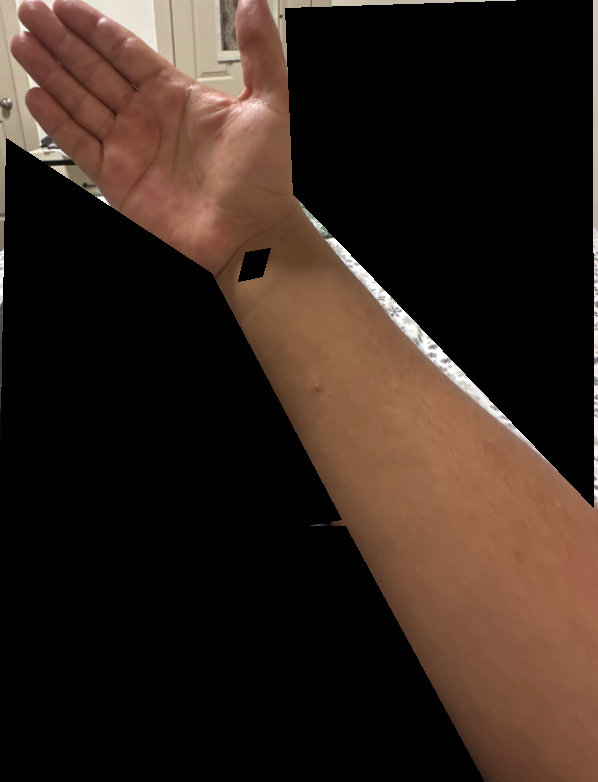The photograph was taken at a distance. Male patient, age 18–29. The affected area is the back of the hand and palm. Favoring Eczema; a more distant consideration is Allergic Contact Dermatitis; less probable is Viral Exanthem.